A male patient, about 70 years old · this is a dermoscopic photograph of a skin lesion: 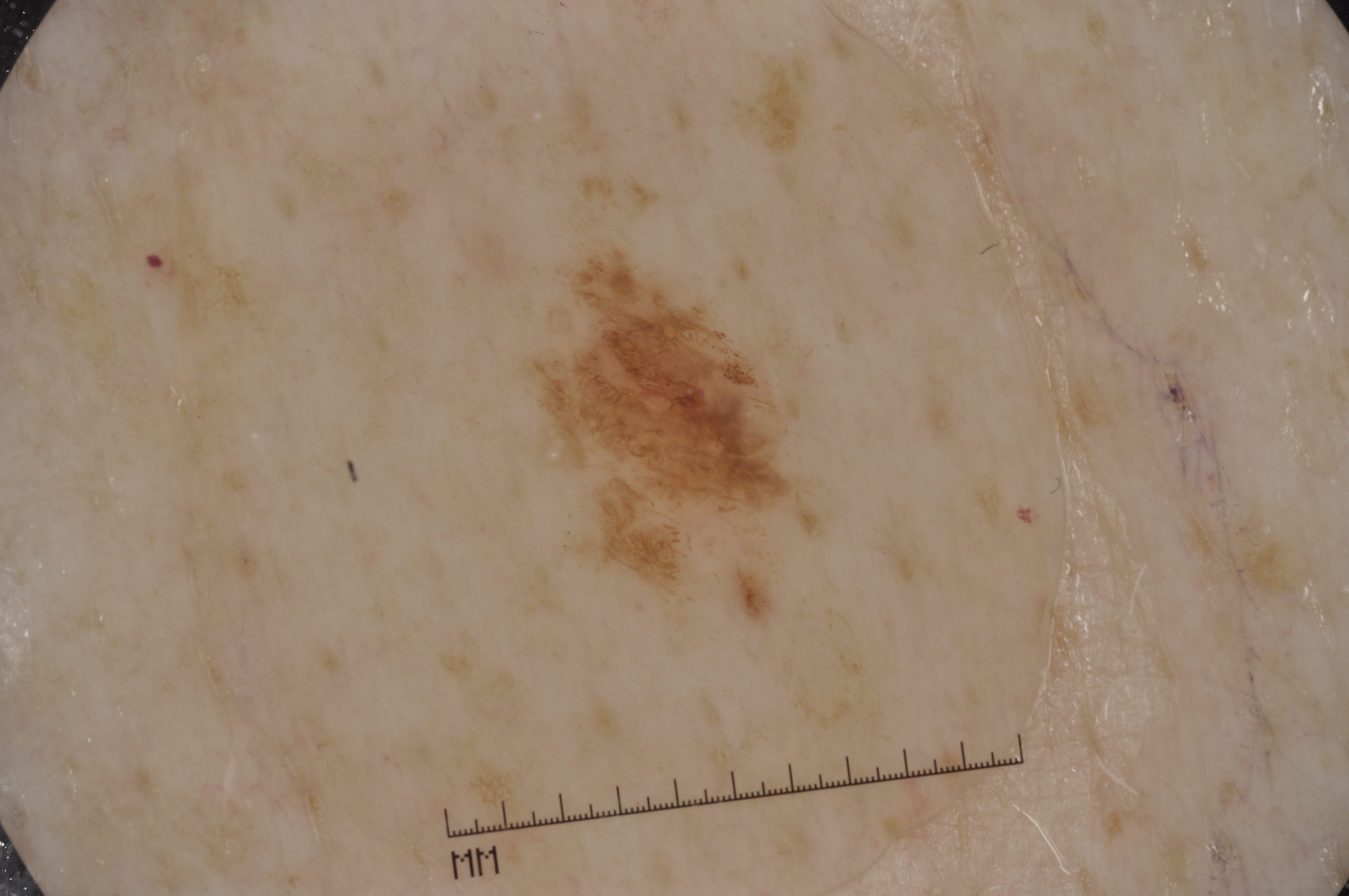Image and clinical context: A small lesion occupying a minor part of the field. Dermoscopic review identifies pigment network; no streaks, milia-like cysts, or negative network. The lesion occupies the region x1=514 y1=234 x2=833 y2=629. Conclusion: Diagnosed as a melanocytic nevus.